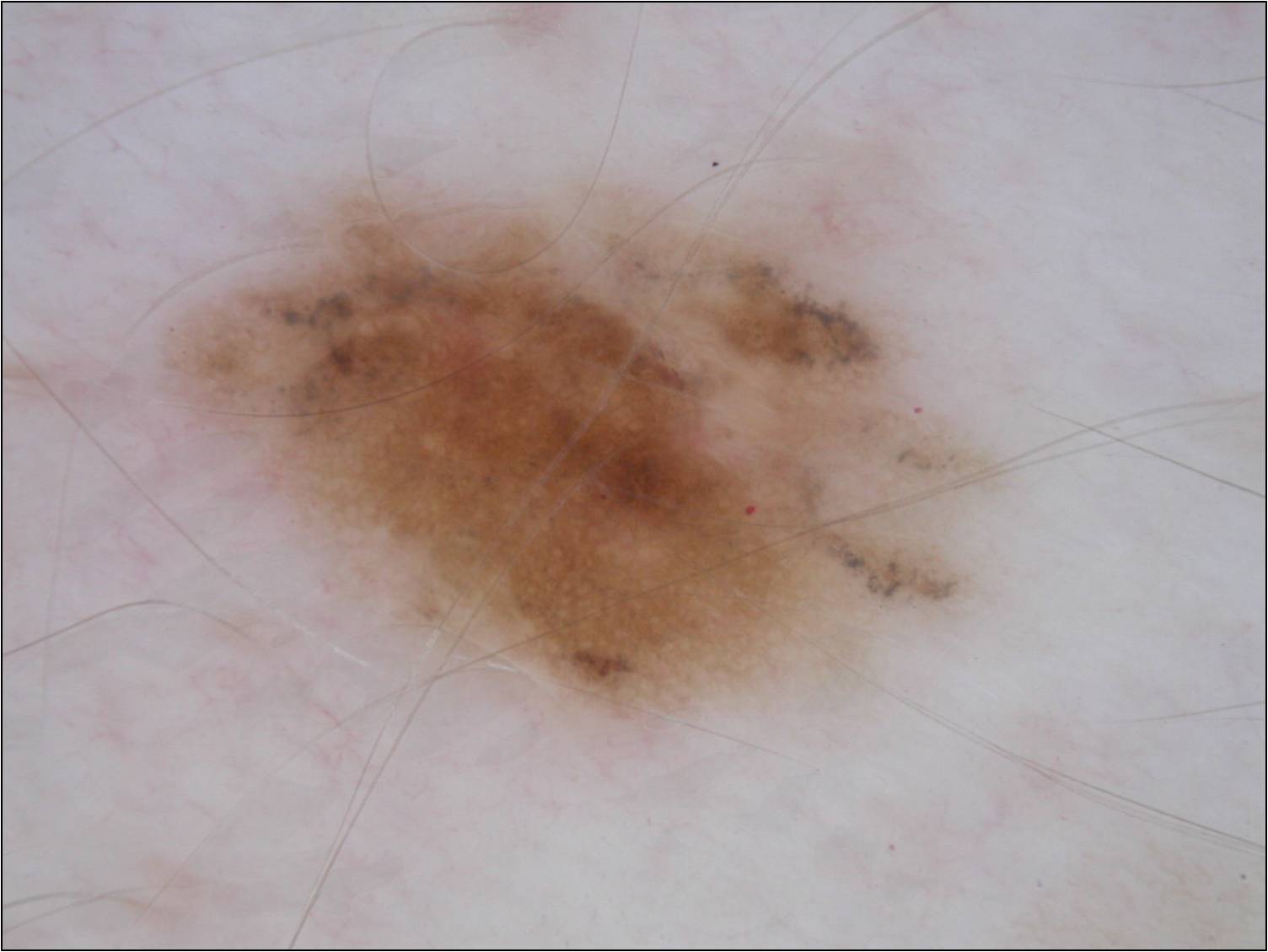Q: How was this image acquired?
A: dermatoscopic image of a skin lesion
Q: What are the patient's age and sex?
A: male, aged 28-32
Q: What dermoscopic features are present?
A: pigment network; absent: milia-like cysts, streaks, negative network, and globules
Q: Lesion extent?
A: moderate
Q: Where is the lesion in the image?
A: (164, 189, 981, 717)
Q: What did the assessment conclude?
A: a melanocytic nevus, a benign skin lesion